The patient says their skin reddens painfully with sun exposure. A dermoscopic image of a skin lesion. The patient describes having a moderate number of moles. A female patient 81 years old. Acquired for a research image collection, with no referral diagnosis: 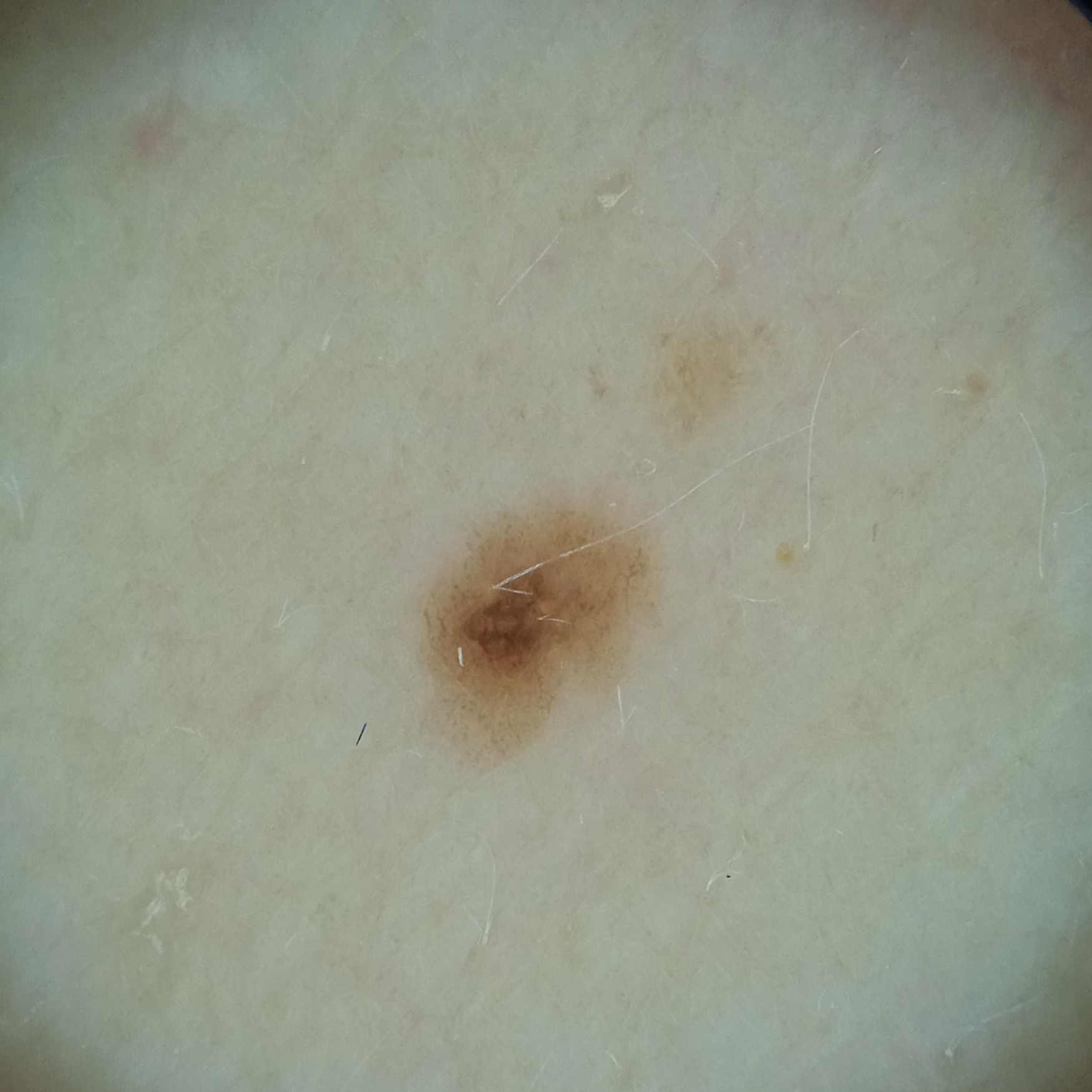The dermatologists' assessment was a melanocytic nevus.